By self-report, a personal history of cancer; the patient describes having numerous moles; a male patient aged 73; a clinical photograph showing a skin lesion: 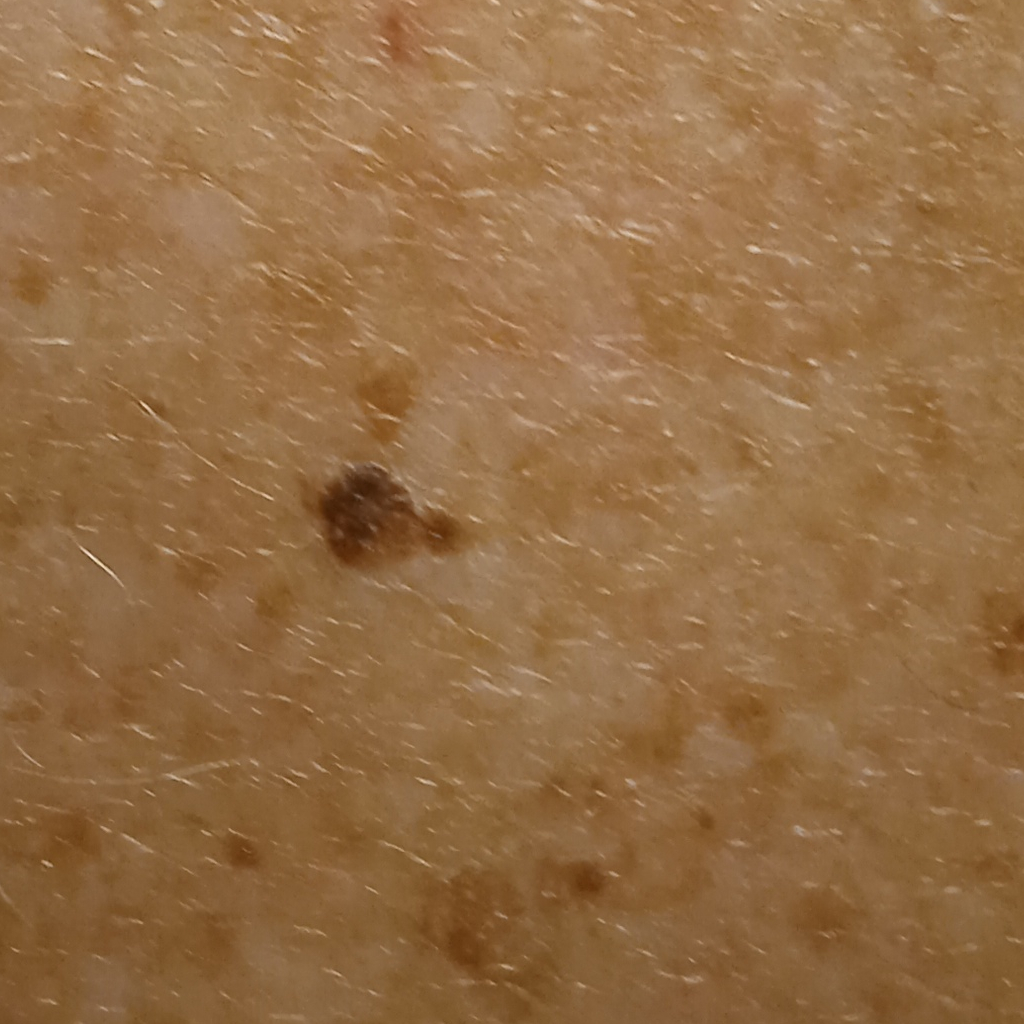The lesion involves the back. Dermatologist review favored a seborrheic keratosis.